The photograph is a close-up of the affected area · the affected area is the arm — 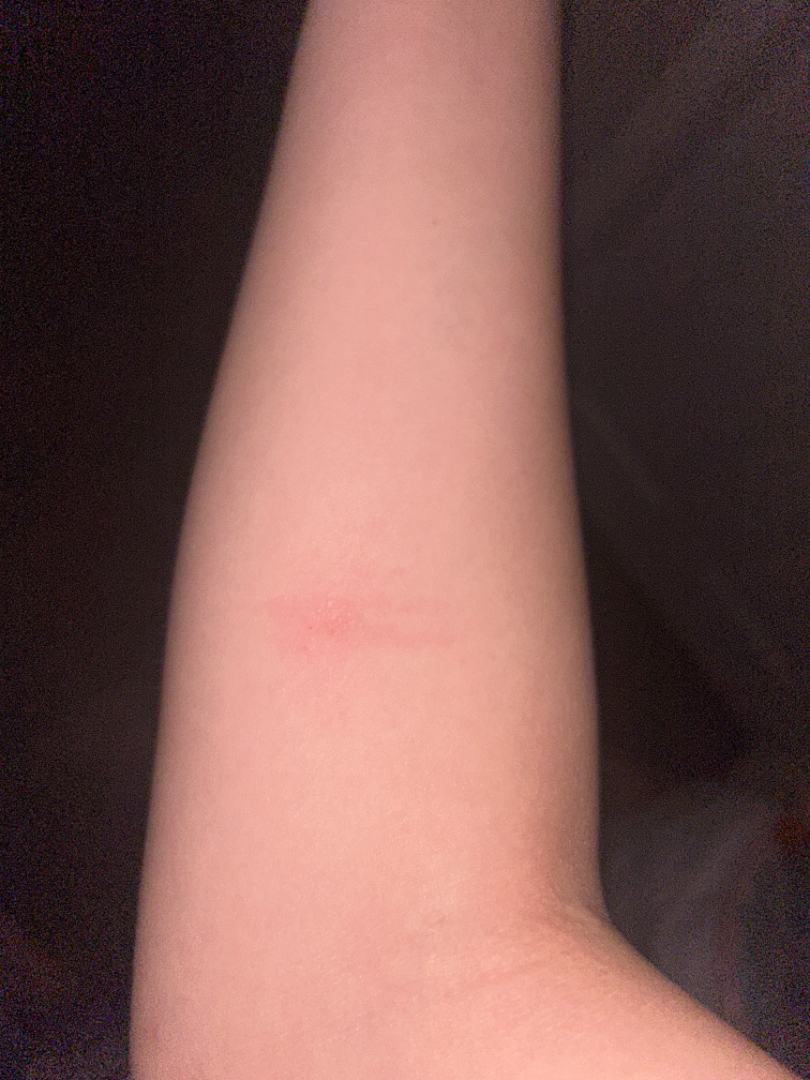Review:
The case was difficult to assess from the available photograph.